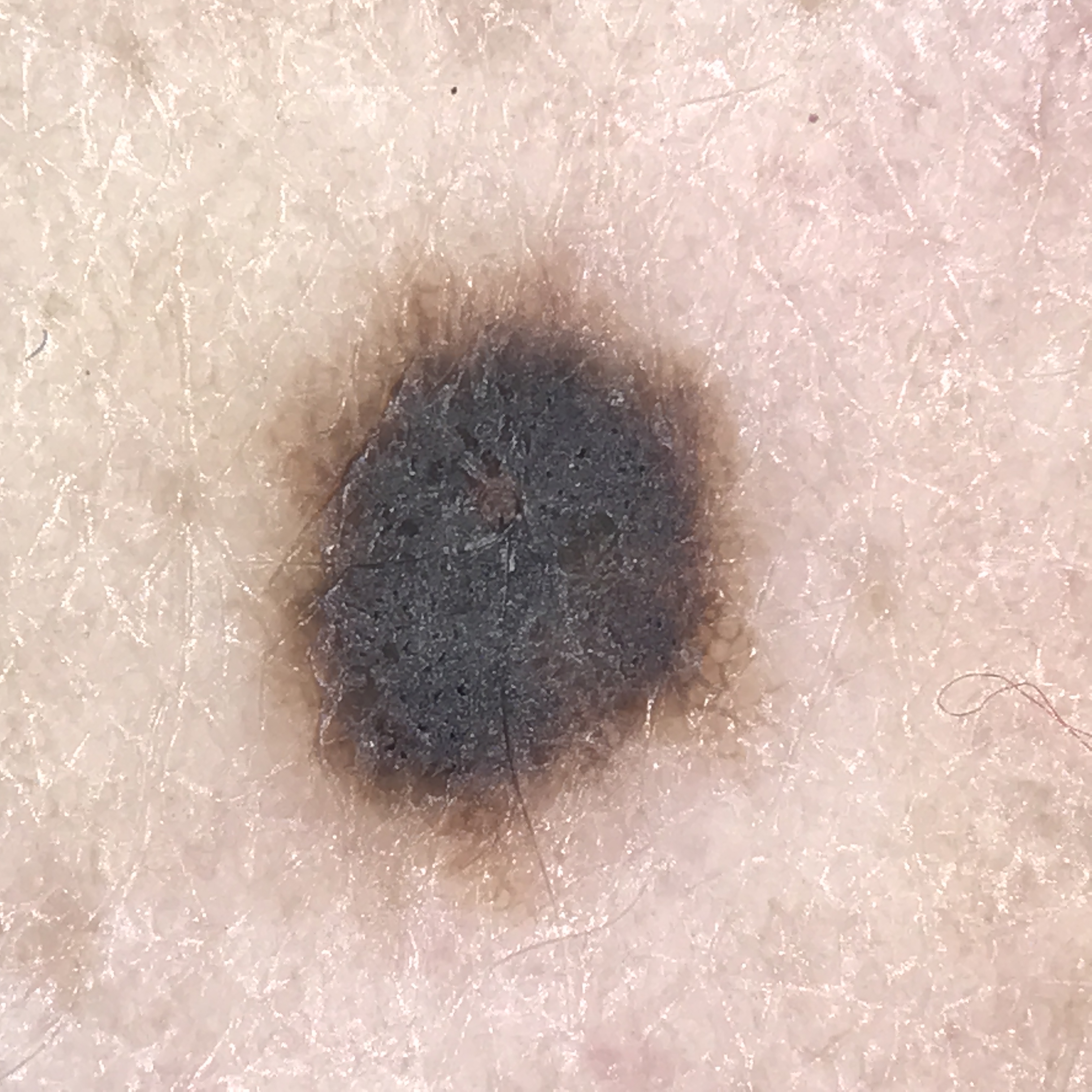* image: dermatoscopy
* class: dysplastic compound nevus (expert consensus)